A dermoscopic photograph of a skin lesion.
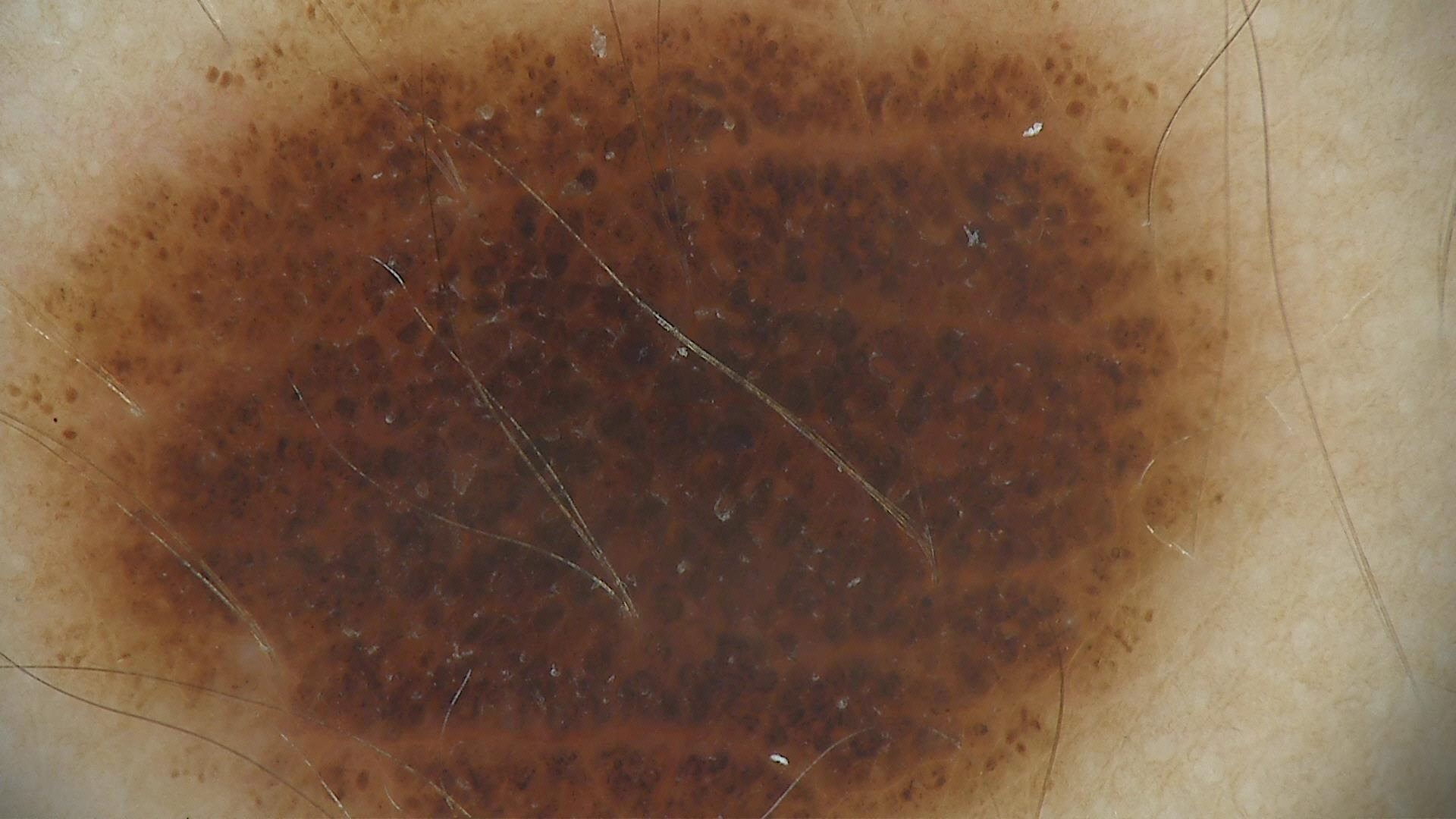diagnostic label: congenital compound nevus (expert consensus)